The affected area is the leg, the photograph was taken at an angle — 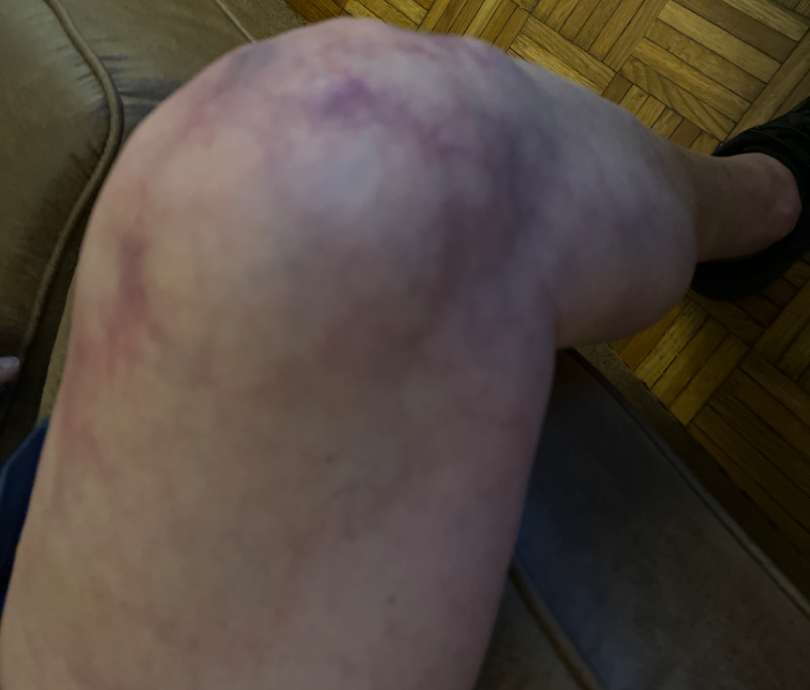Findings:
- assessment — indeterminate from the photograph
- lesion symptoms — darkening and bothersome appearance